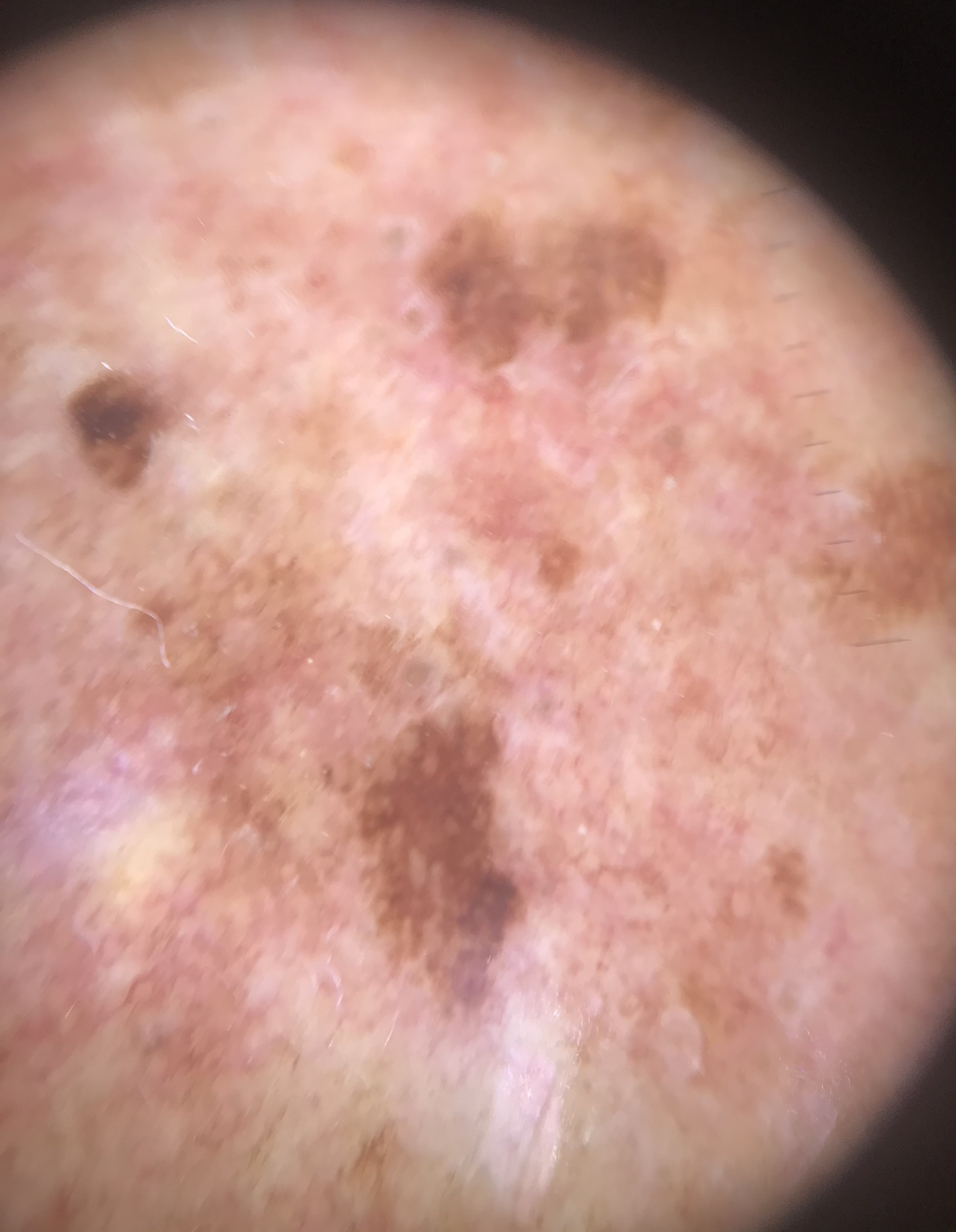Dermoscopy of a skin lesion. The morphology is that of a keratinocytic lesion. Classified as a seborrheic keratosis.